Skin type II · a male subject about 70 years old — 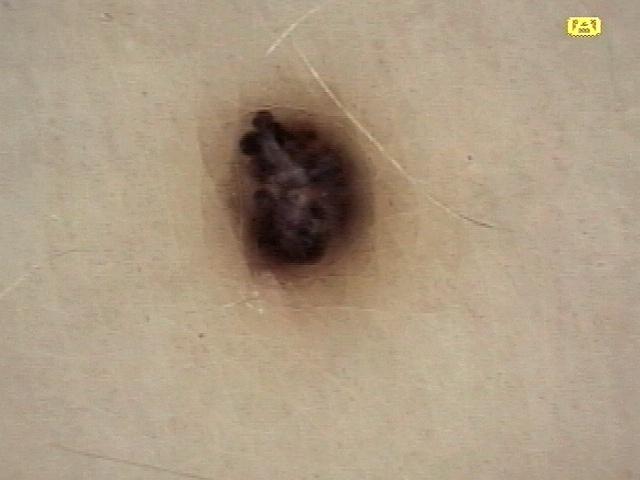{
  "diagnosis": {
    "name": "vascular lesion",
    "malignancy": "benign",
    "confirmation": "expert clinical impression"
  }
}